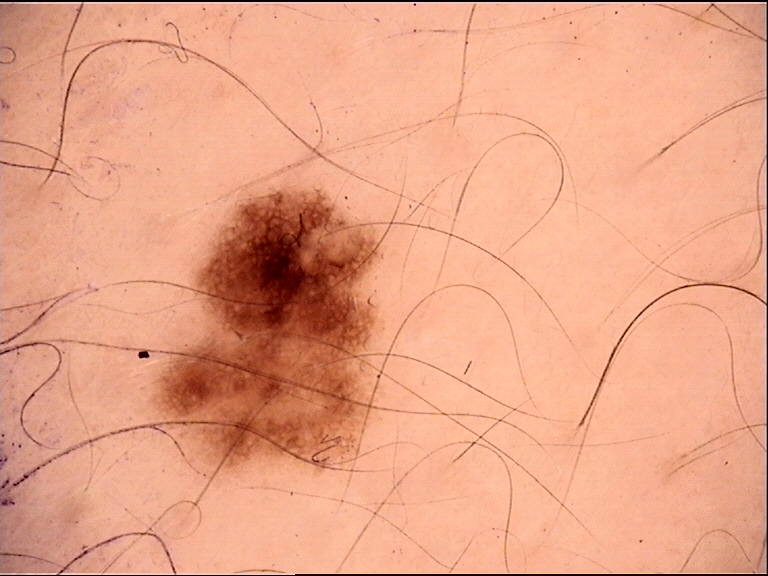  image: dermatoscopy
  diagnosis:
    name: dysplastic junctional nevus
    code: jd
    malignancy: benign
    super_class: melanocytic
    confirmation: expert consensus